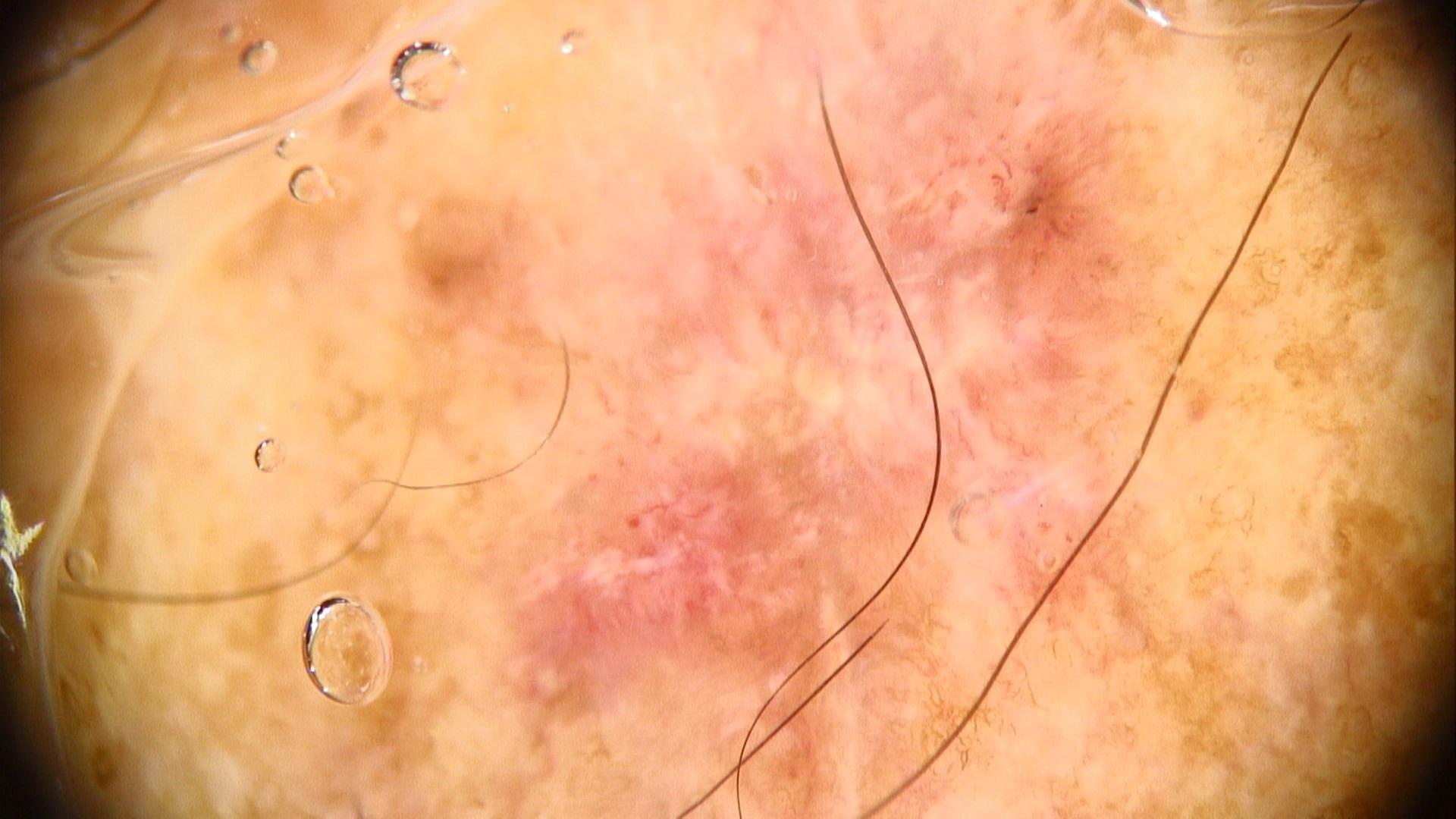A male patient aged 68-72.
The lesion involves a lower extremity.
Histopathological examination showed a tumor of follicular differentiation — a basal cell carcinoma.